Recorded as Fitzpatrick skin type II · a clinical photograph showing a skin lesion · a female patient in their early 80s: 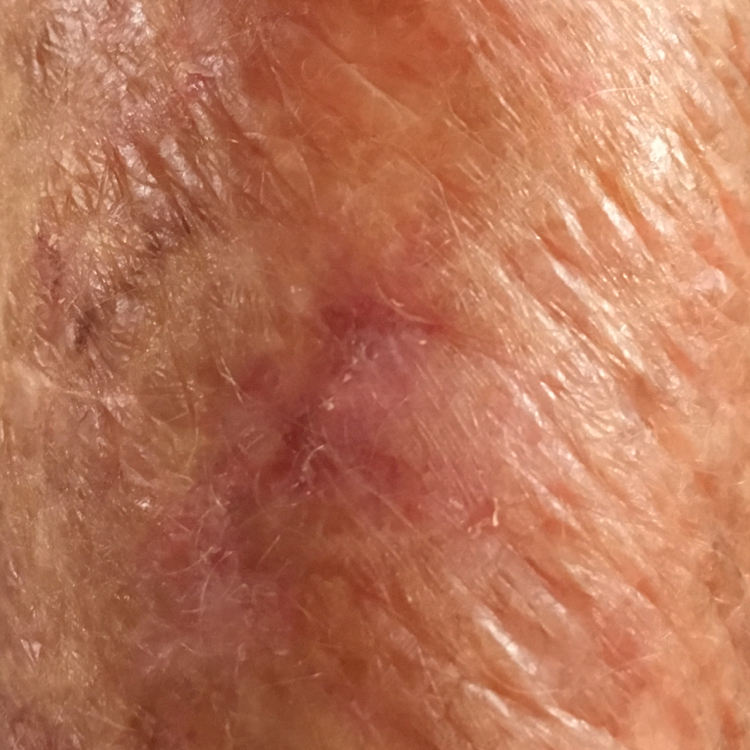The lesion was found on a hand.
The lesion measures approximately 7 × 5 mm.
Histopathological examination showed a malignant lesion — a squamous cell carcinoma.